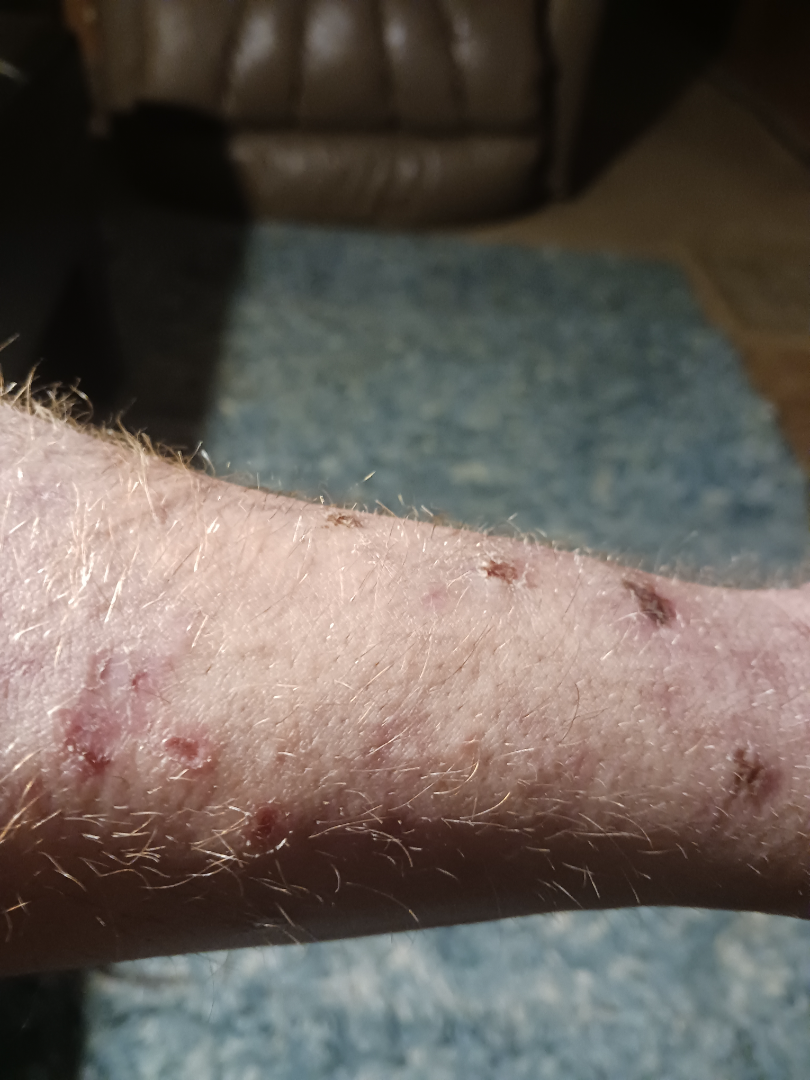<case>
  <assessment>ungradable on photographic review</assessment>
</case>